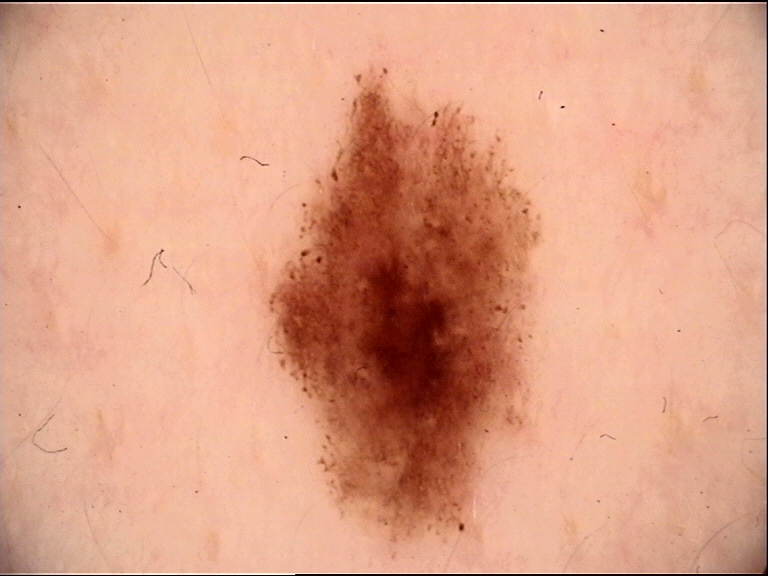A dermoscopic photograph of a skin lesion. The diagnostic label was a benign lesion — a dysplastic junctional nevus.